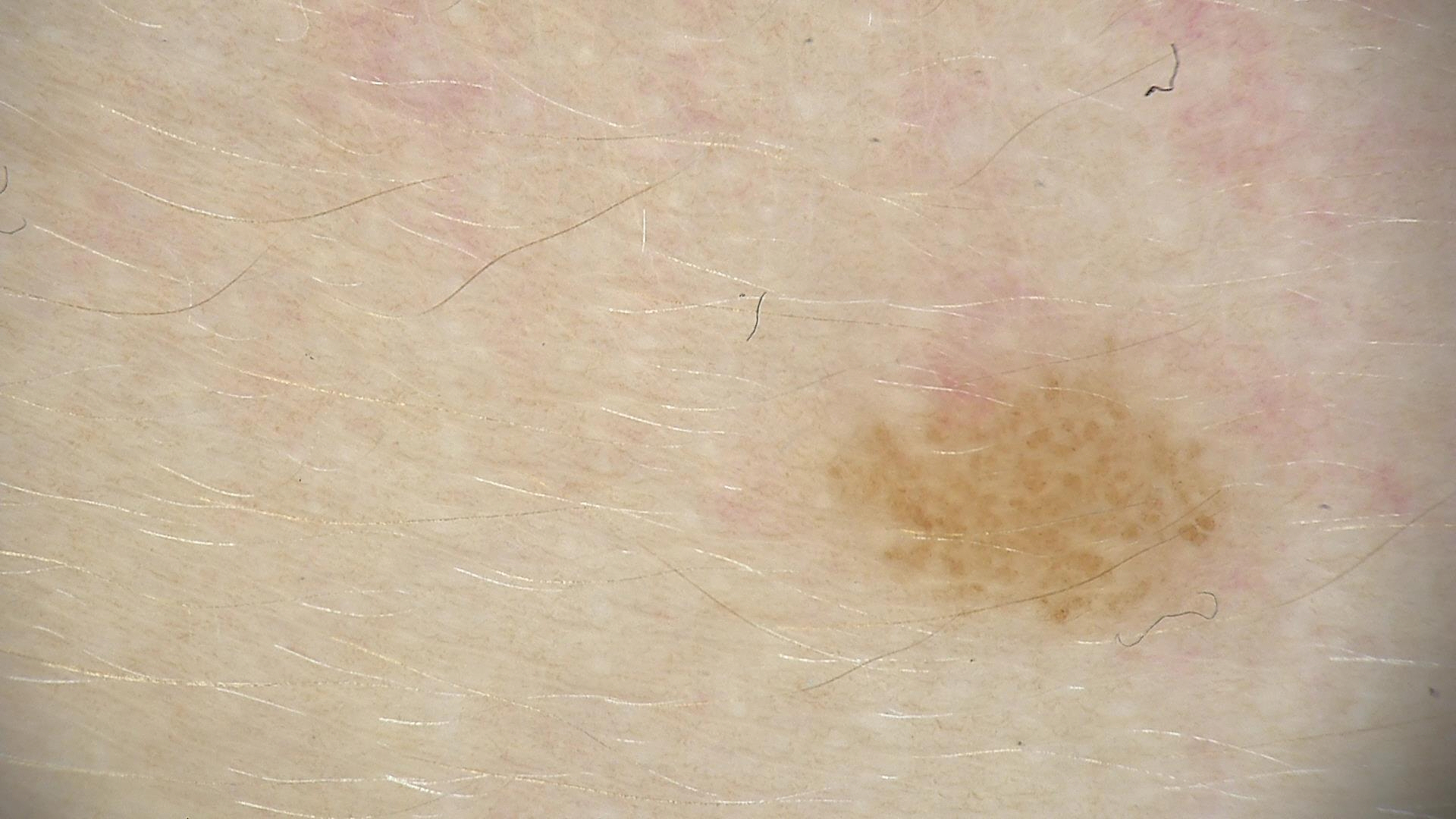Dermoscopy of a skin lesion. The diagnosis was a banal lesion — a compound nevus.